The subject is 40–49, female. The lesion involves the top or side of the foot. This is a close-up image: 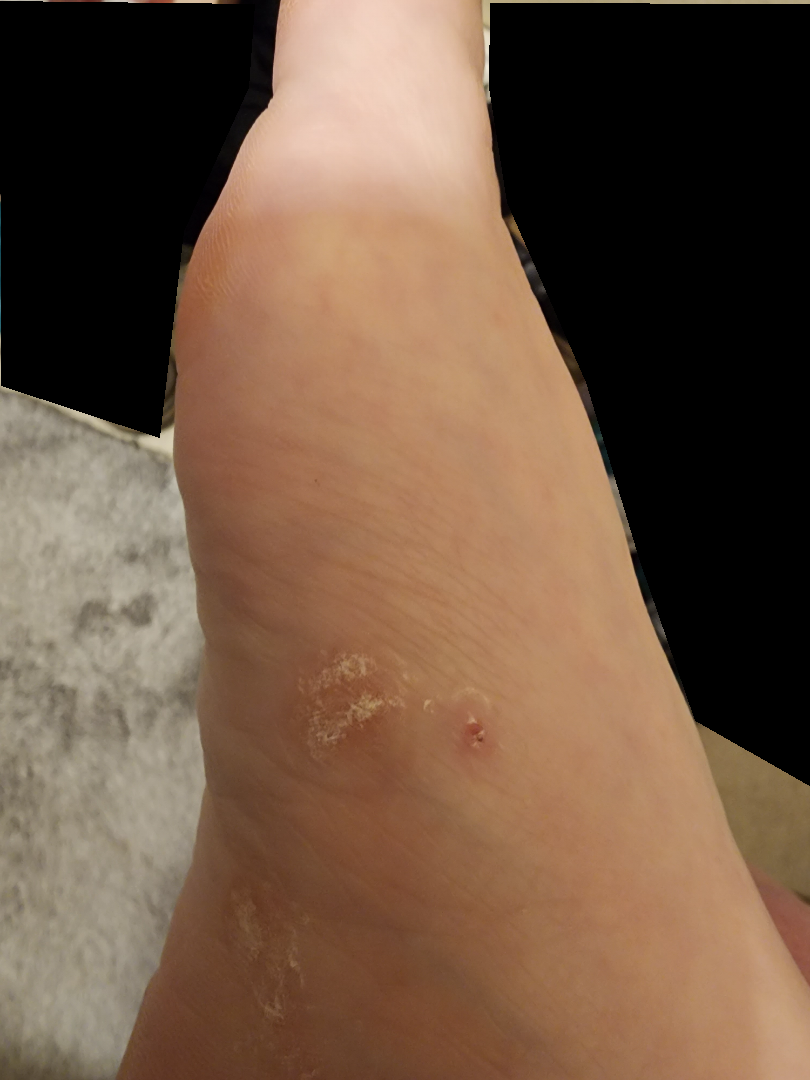Assessment: The image was not sufficient for the reviewer to characterize the skin condition.